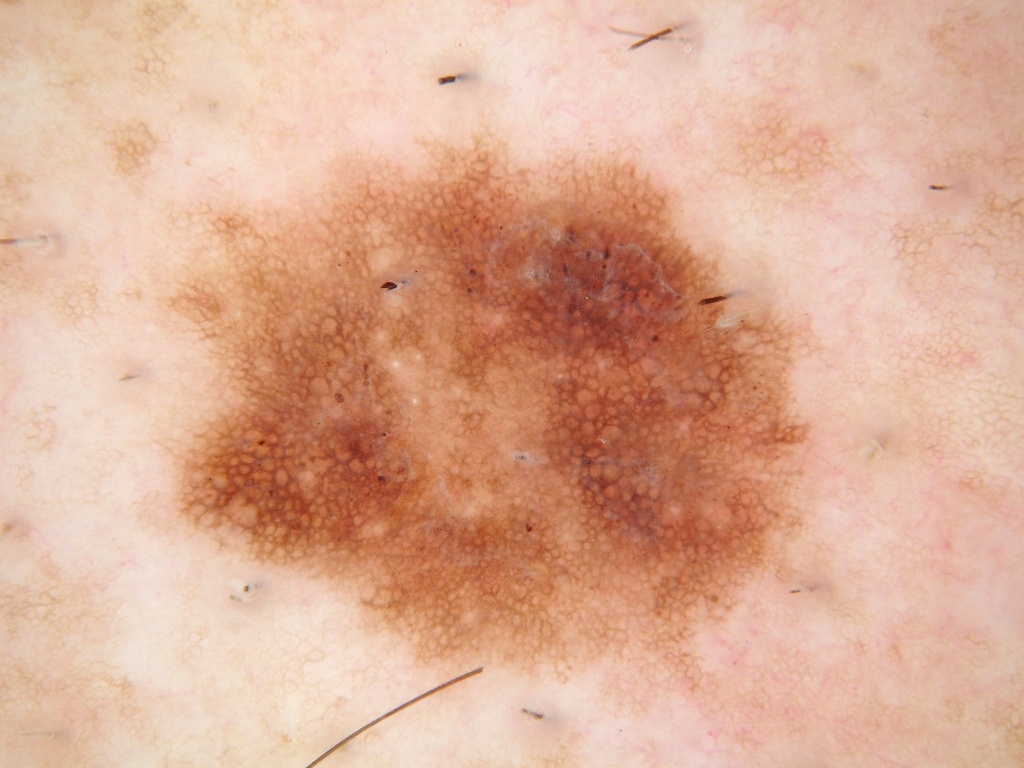  patient:
    sex: male
    age_approx: 45
  image:
    modality: dermoscopy
  lesion_extent: large
  dermoscopic_features:
    present:
      - milia-like cysts
      - pigment network
    absent:
      - negative network
      - streaks
      - globules
  lesion_location:
    bbox_xyxy:
      - 132
      - 119
      - 831
      - 723
  diagnosis:
    name: melanocytic nevus
    malignancy: benign
    lineage: melanocytic
    provenance: clinical